The patient was assessed as skin type III · a smartphone photograph of a skin lesion · a female subject age 77 · by history, prior malignancy (patient or family): 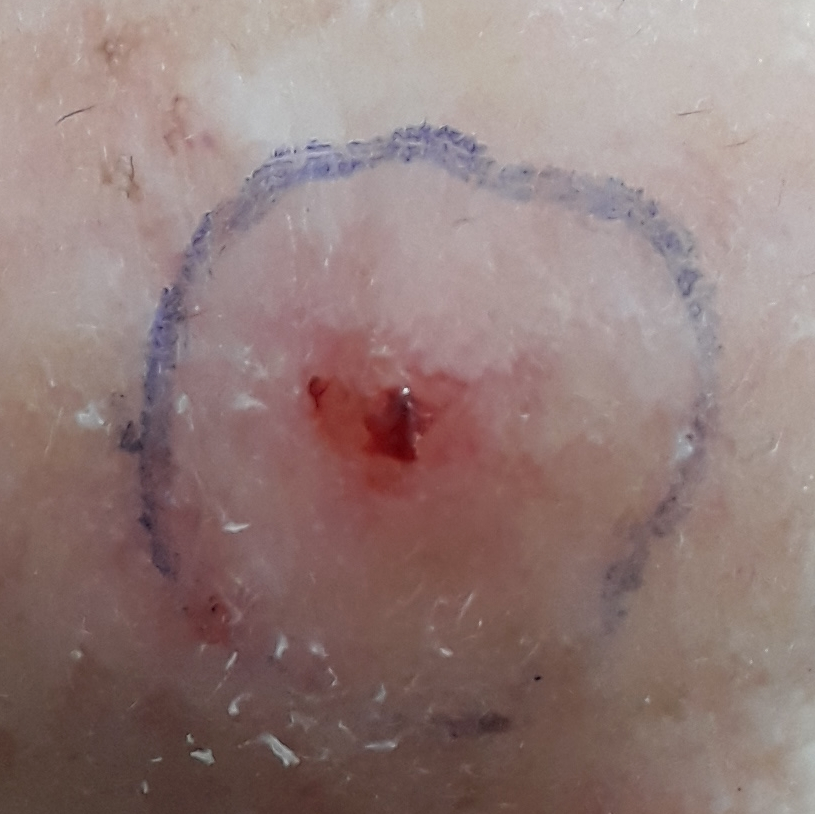Findings: The lesion is located on a forearm. The lesion measures approximately 11 × 6 mm. Per patient report, the lesion is elevated, has grown, has bled, and itches. Diagnosis: Histopathology confirmed an actinic keratosis.